The affected area is the leg and top or side of the foot. The contributor reports the lesion is rough or flaky and raised or bumpy. This is a close-up image. Reported duration is one to four weeks. The lesion is associated with itching. The patient described the issue as a rash.
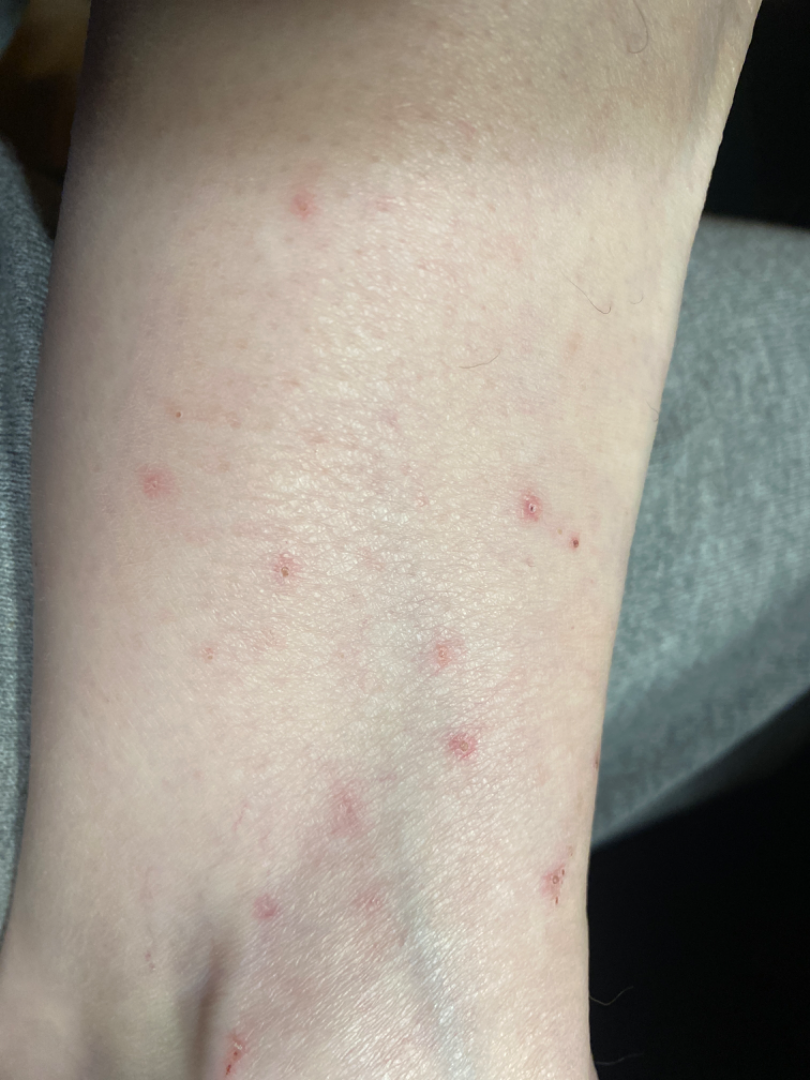Notes:
* differential: the primary impression is Eczema; an alternative is Hypersensitivity